Dermoscopy of a skin lesion: 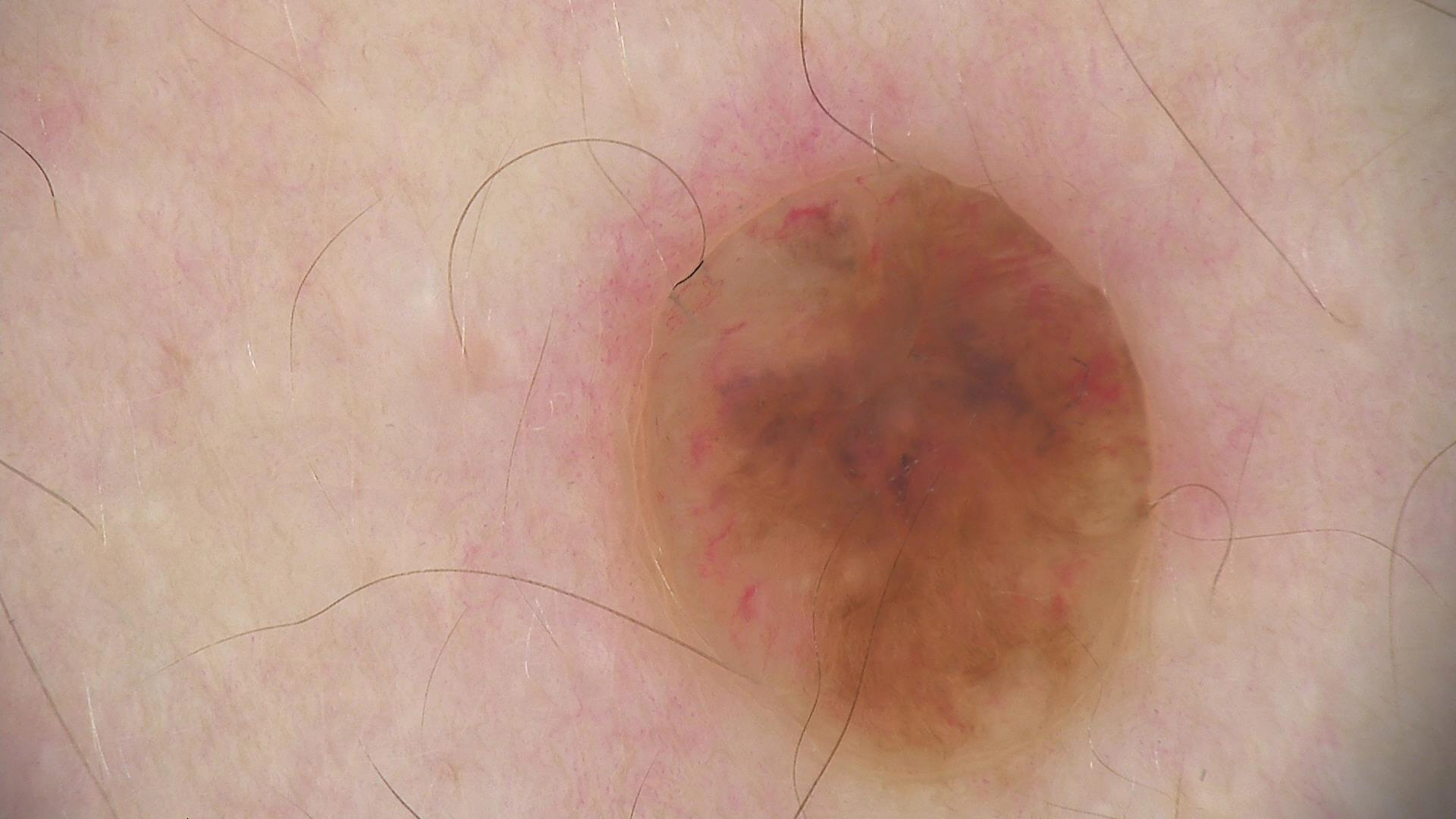The diagnostic label was a banal lesion — a dermal nevus.